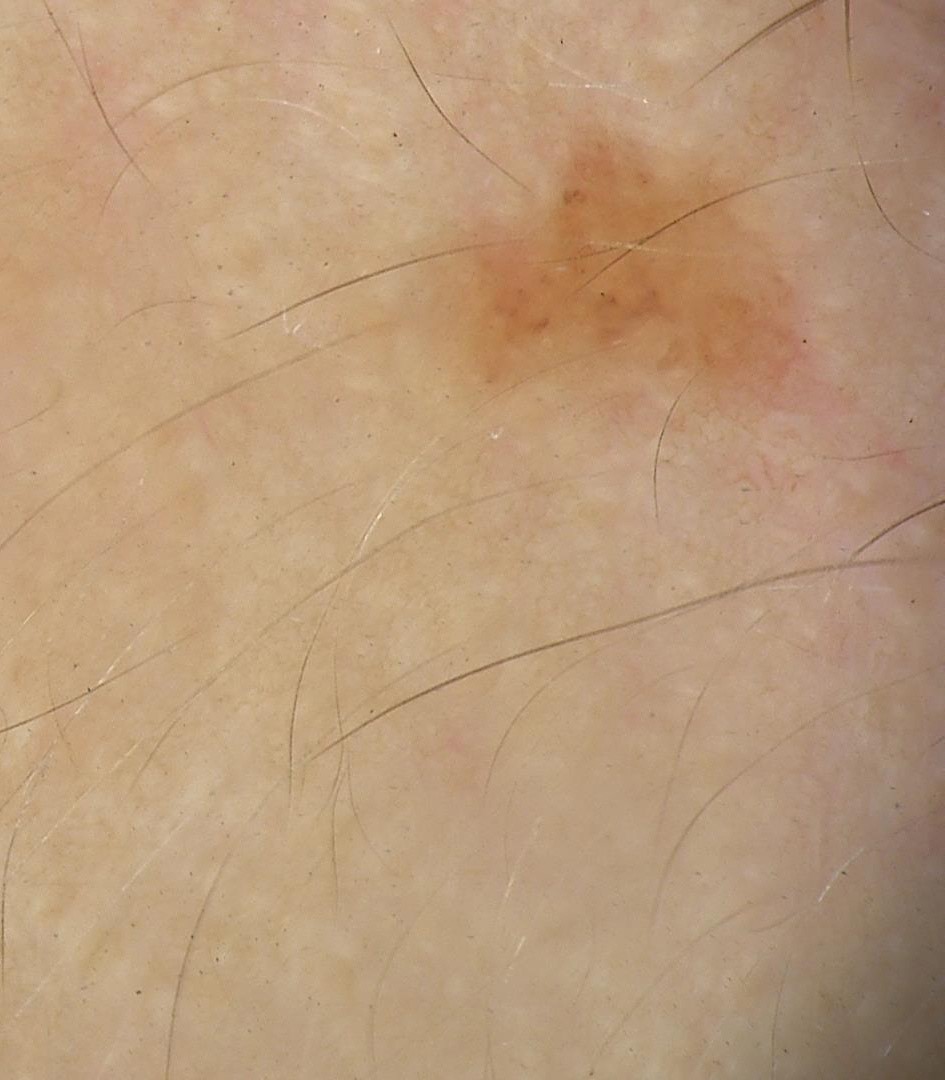A dermoscopic close-up of a skin lesion.
The diagnostic label was a lentigo simplex.